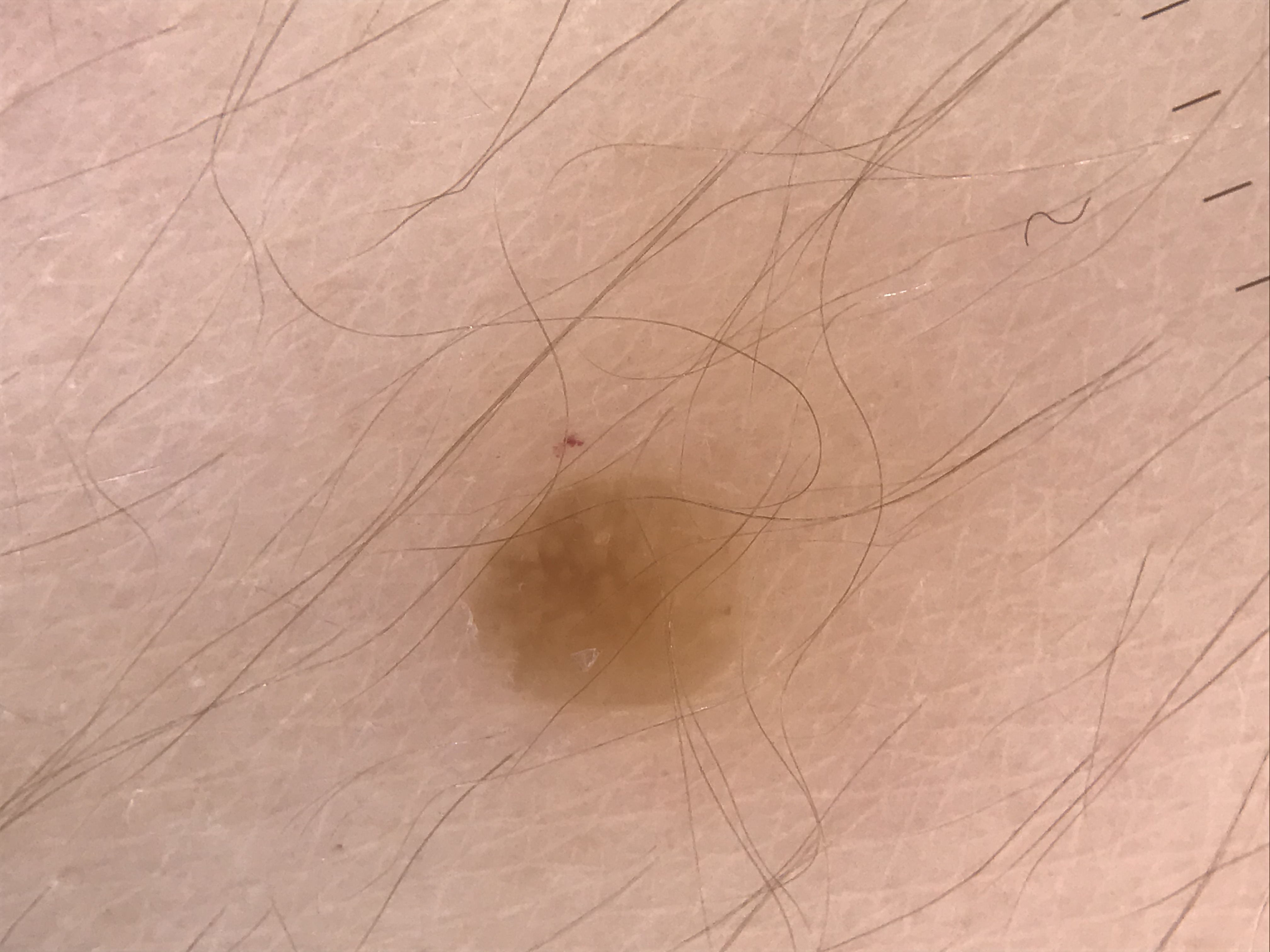assessment: seborrheic keratosis (expert consensus).